Located on the leg; the patient is 18–29, female; close-up view:
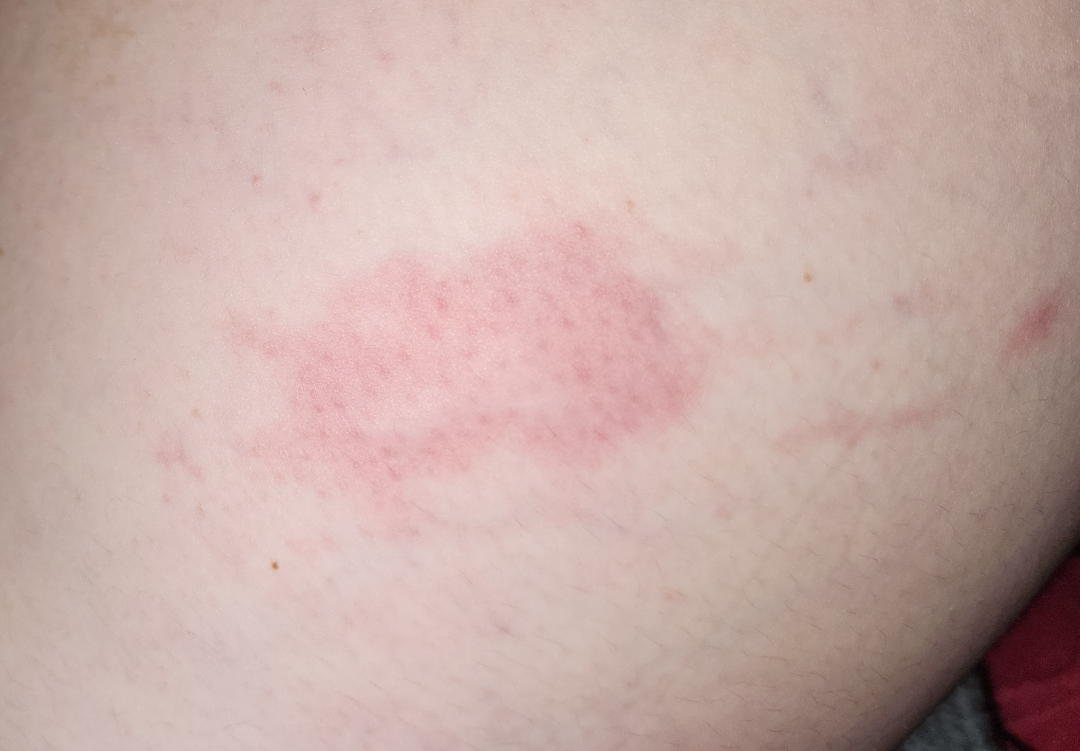Diagnostic features were not clearly distinguishable in this photograph. The condition has been present for about one day. The lesion is associated with bothersome appearance, burning, enlargement, darkening and pain. The patient also reports joint pain, fatigue and shortness of breath.